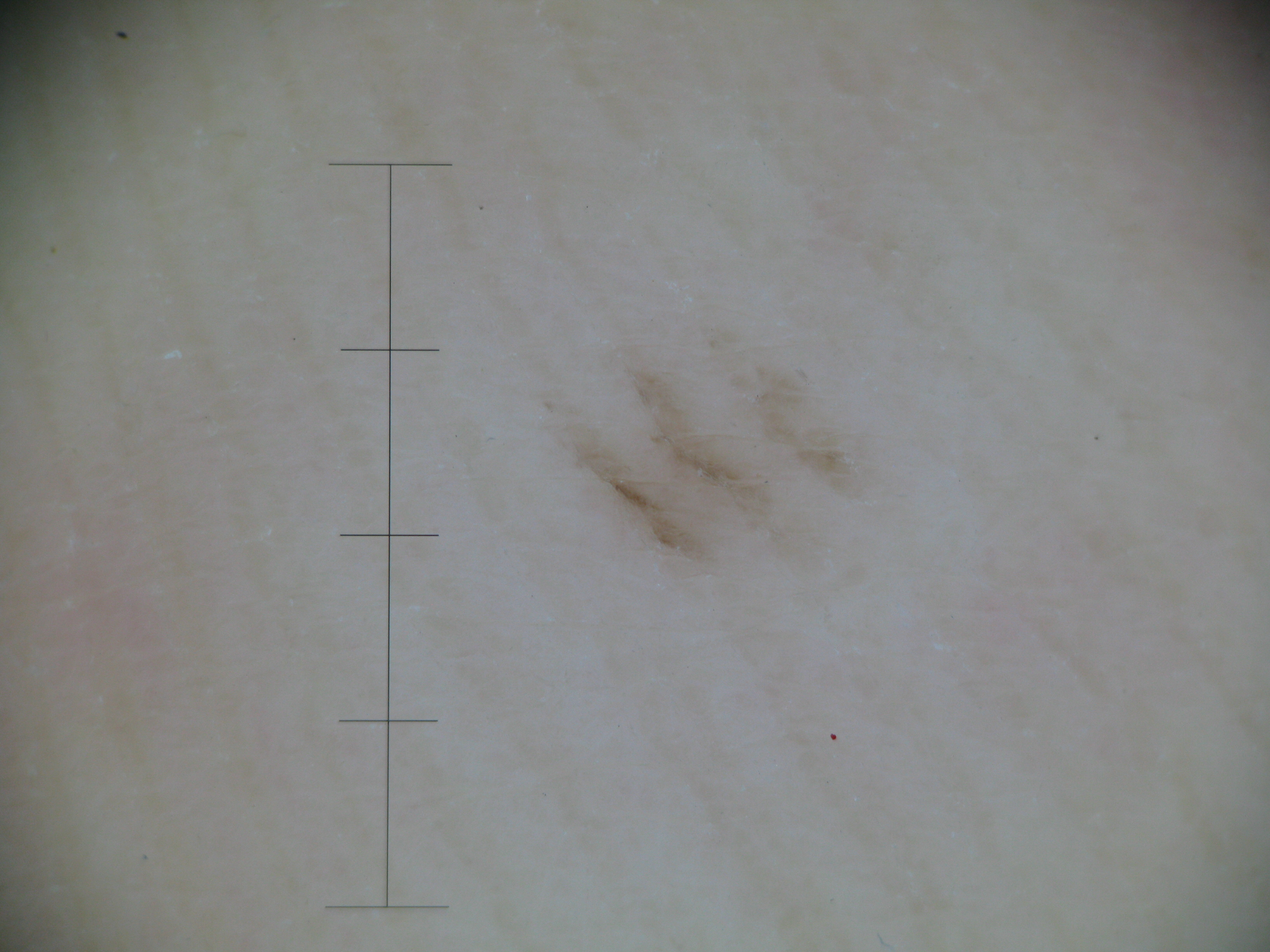Labeled as an acral junctional nevus.